The lesion involves the arm, an image taken at a distance:
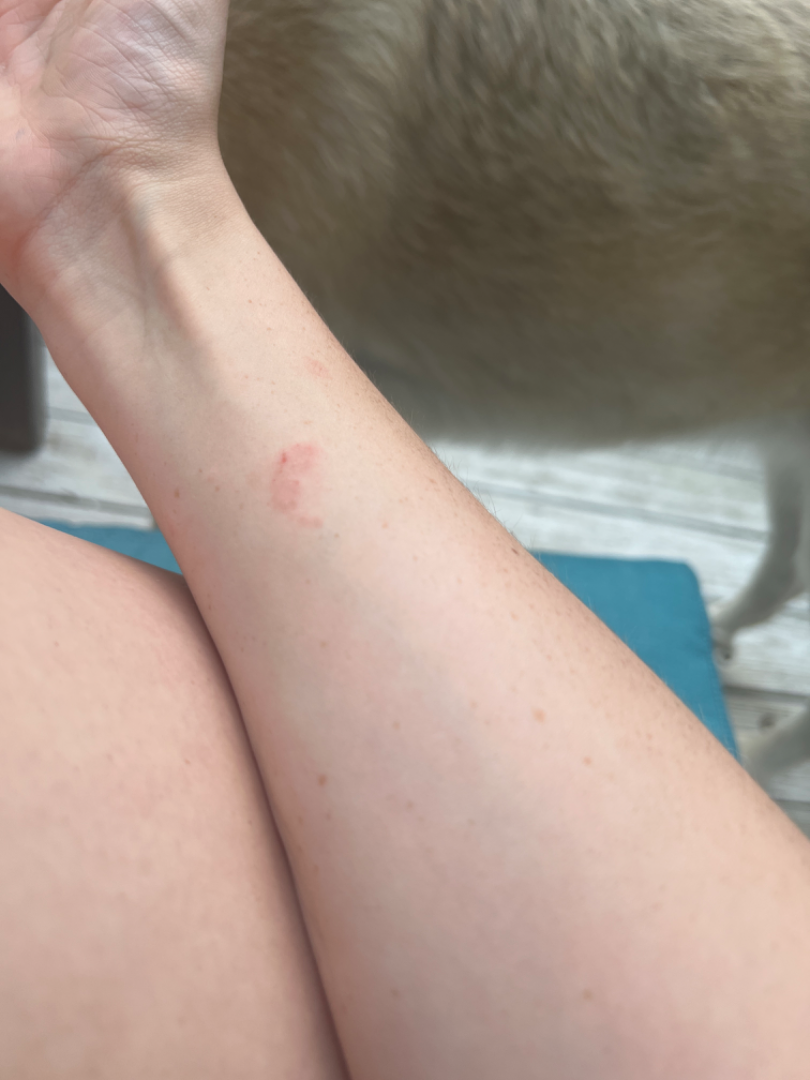The skin findings could not be characterized from the image. Skin tone: FST III; non-clinician graders estimated Monk Skin Tone 2 or 3 (two reviewer pools). The lesion is associated with burning, itching, enlargement and bleeding. No relevant systemic symptoms. Texture is reported as raised or bumpy. The patient described the issue as a rash. Present for one to four weeks.